A dermoscopic view of a skin lesion. The patient is a female approximately 45 years of age: 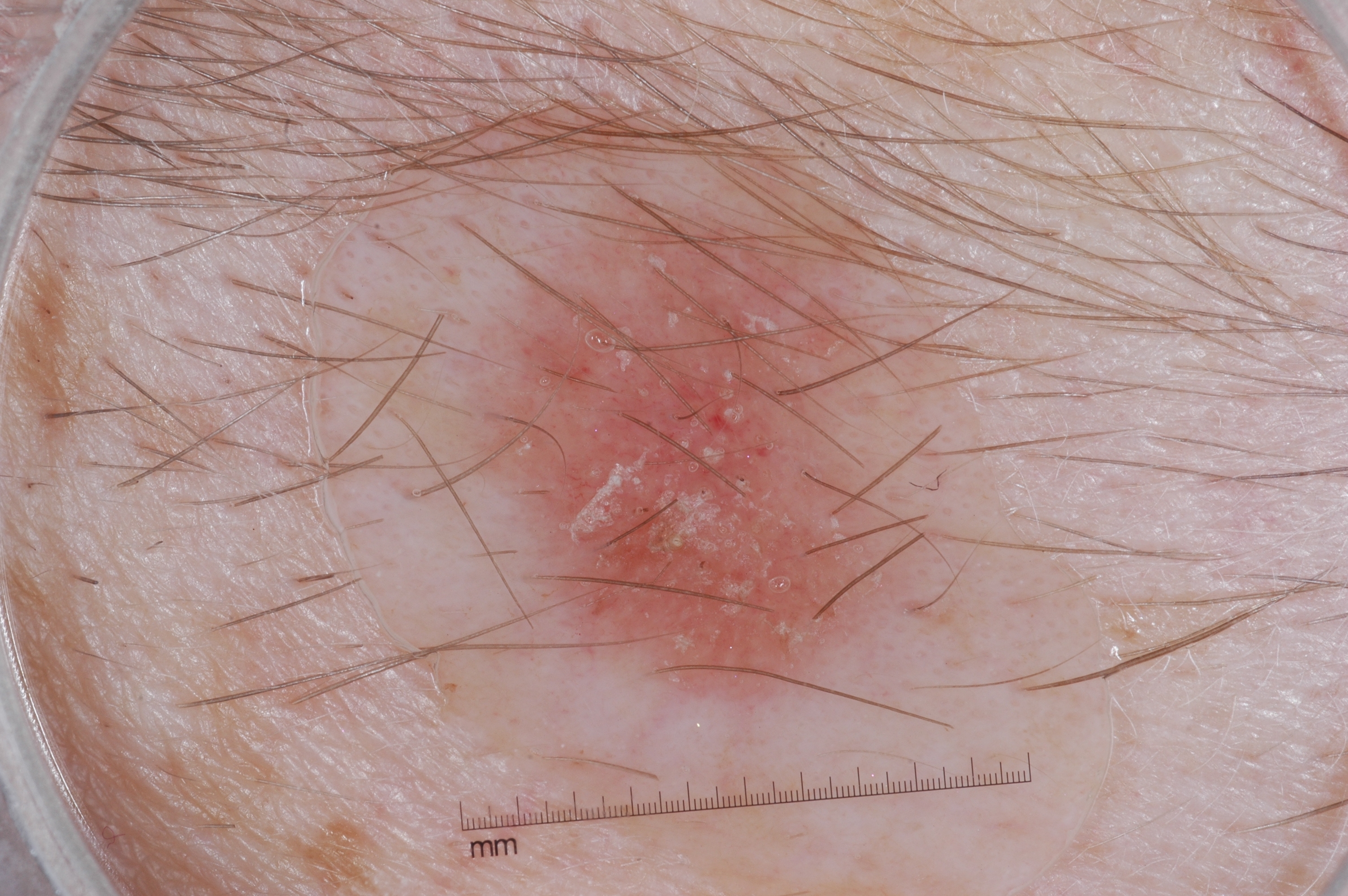Notes:
* absent dermoscopic features: milia-like cysts, streaks, negative network, and pigment network
* extent: ~15% of the field
* location: box(464, 154, 937, 700)
* impression: a seborrheic keratosis